A dermoscopic photograph of a skin lesion.
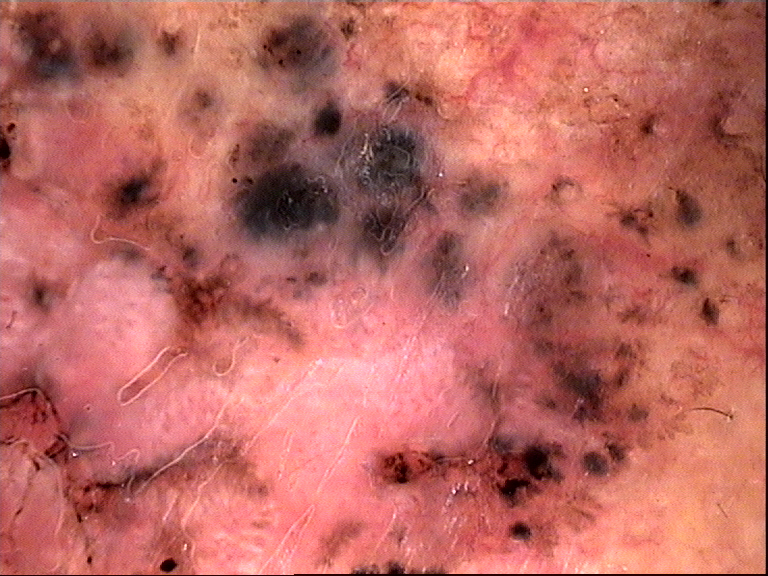Histopathologically confirmed as a basal cell carcinoma.